Acquired for a research image collection, with no referral diagnosis; dermoscopy of a skin lesion; the patient reports a personal history of skin cancer and a personal history of cancer; a moderate number of moles by the patient's own estimate.
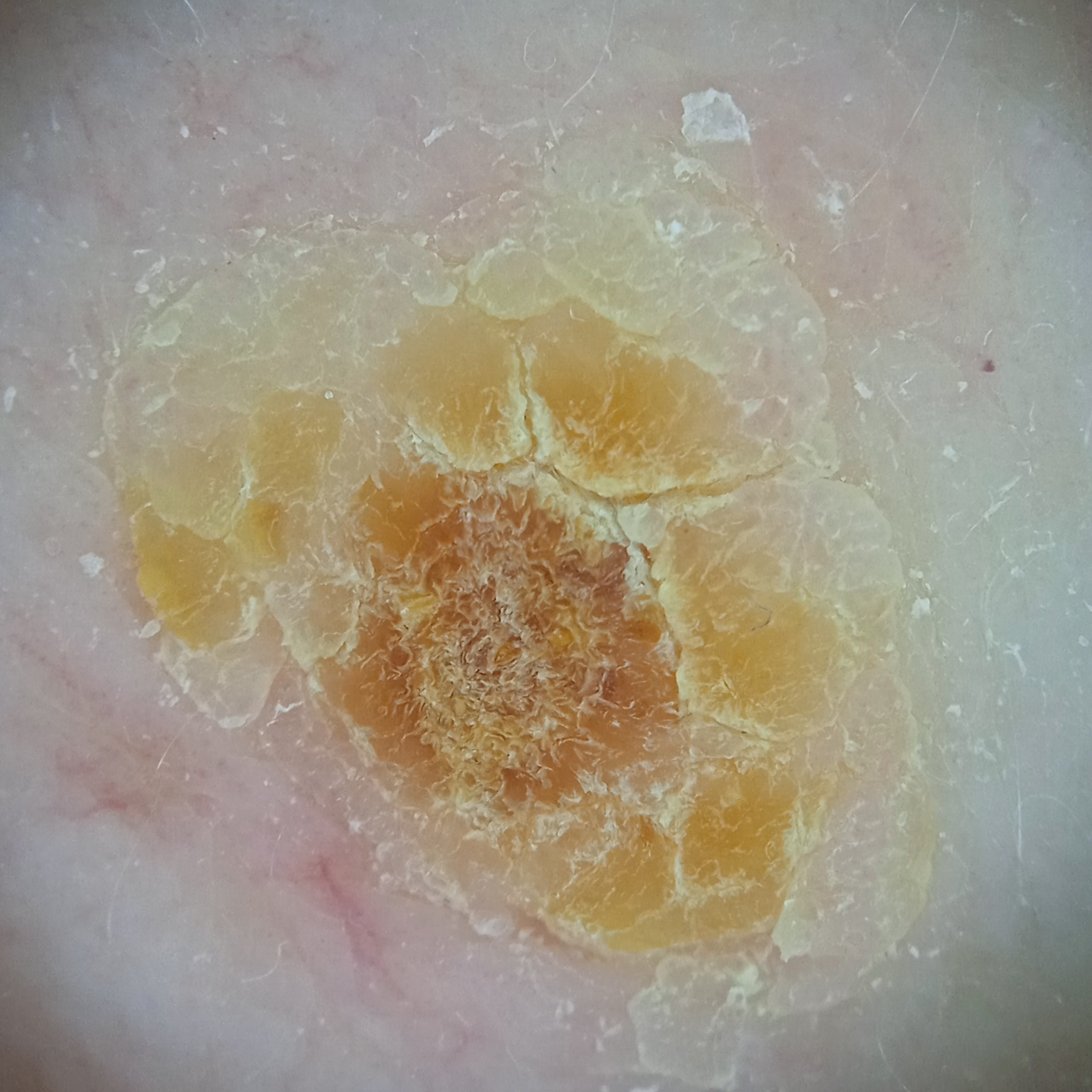<record>
<lesion_size>
<diameter_mm>11.1</diameter_mm>
</lesion_size>
<diagnosis>
<name>actinic keratosis</name>
<malignancy>benign</malignancy>
<unanimous>false</unanimous>
<certainty>moderate</certainty>
</diagnosis>
</record>